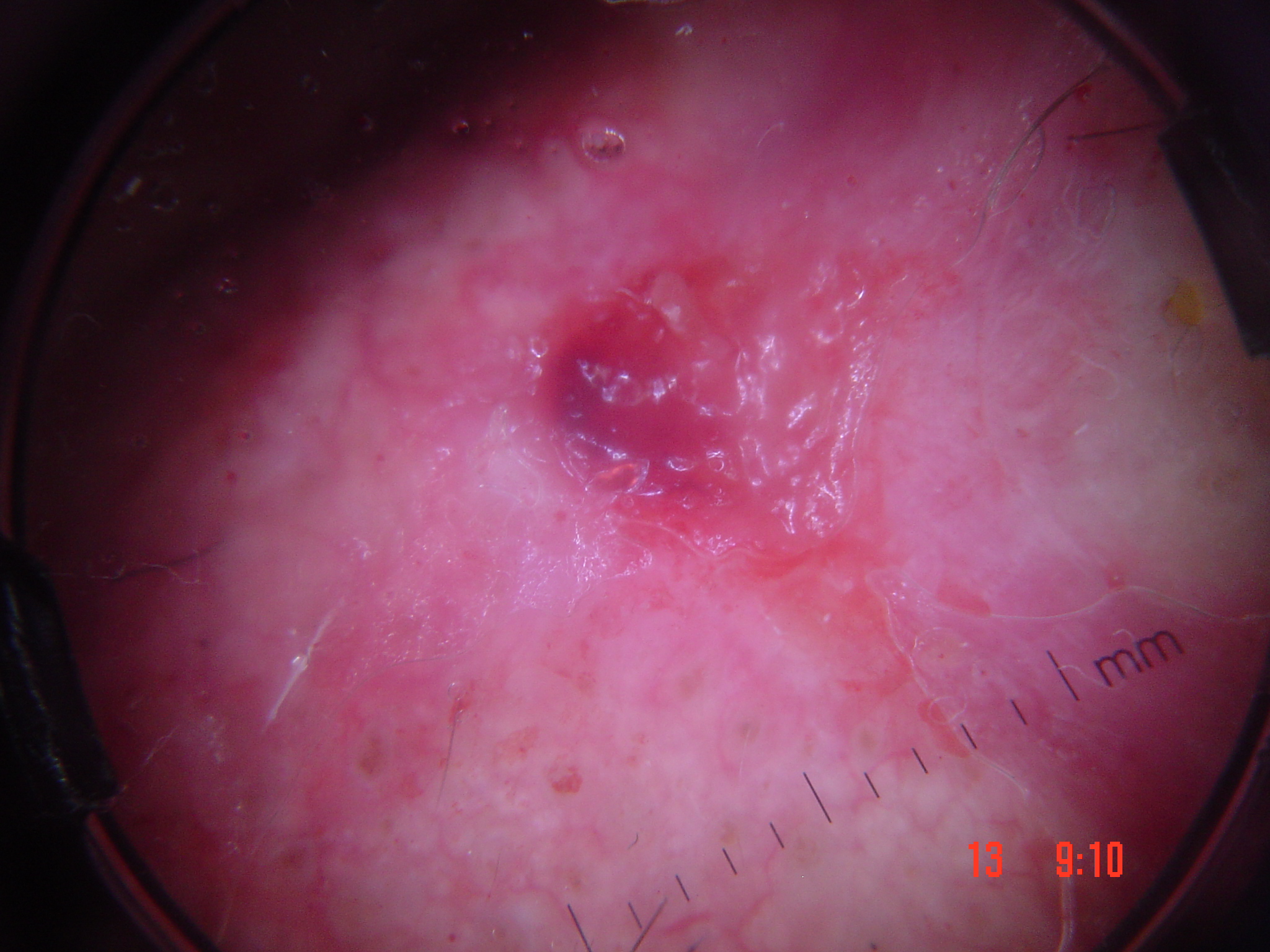image type: dermoscopy
subtype: keratinocytic
diagnostic label: squamous cell carcinoma (biopsy-proven)